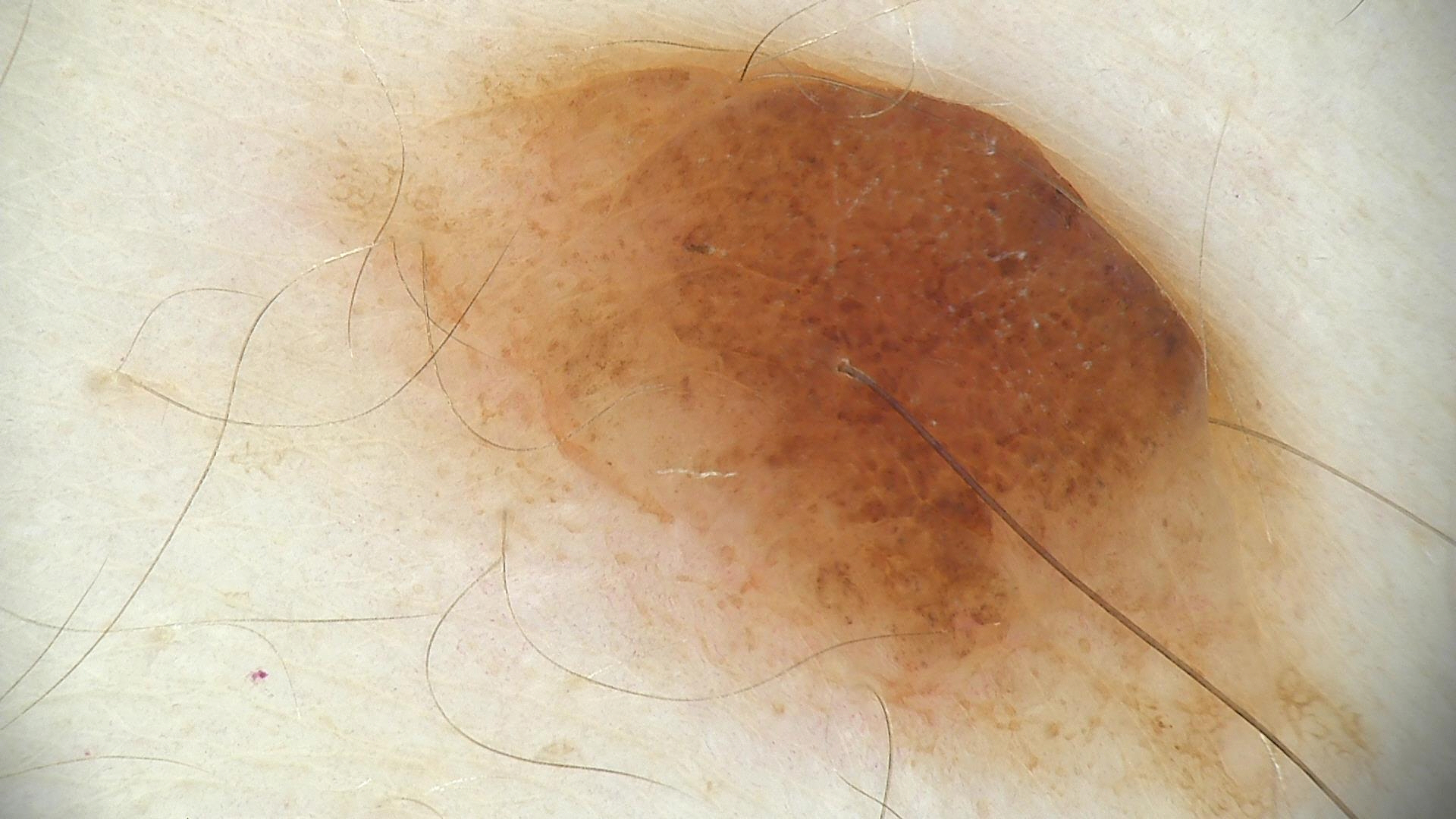Findings:
The morphology is that of a banal lesion.
Conclusion:
The diagnosis was a compound nevus.